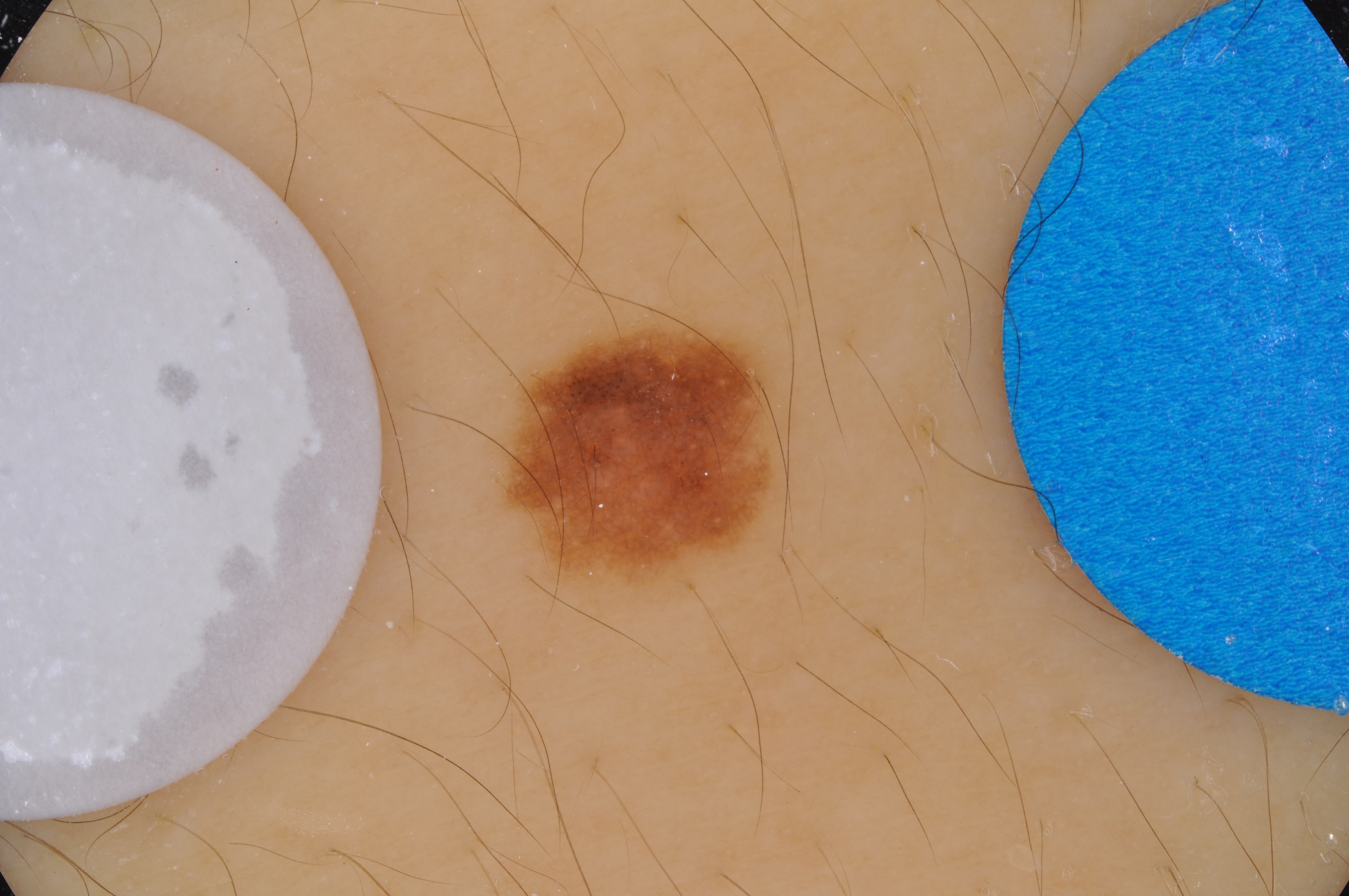patient:
  sex: male
  age_approx: 15
image:
  modality: dermoscopy
dermoscopic_features:
  present:
    - pigment network
  absent:
    - negative network
    - milia-like cysts
    - streaks
lesion_location:
  bbox_xyxy:
    - 486
    - 308
    - 791
    - 603
lesion_extent:
  approx_field_fraction_pct: 6
diagnosis:
  name: melanocytic nevus
  malignancy: benign
  lineage: melanocytic
  provenance: clinical